Reported lesion symptoms include itching and burning; the lesion is described as rough or flaky and raised or bumpy; the condition has been present for about one day; the back of the torso is involved; a close-up photograph; female subject, age 40–49 — 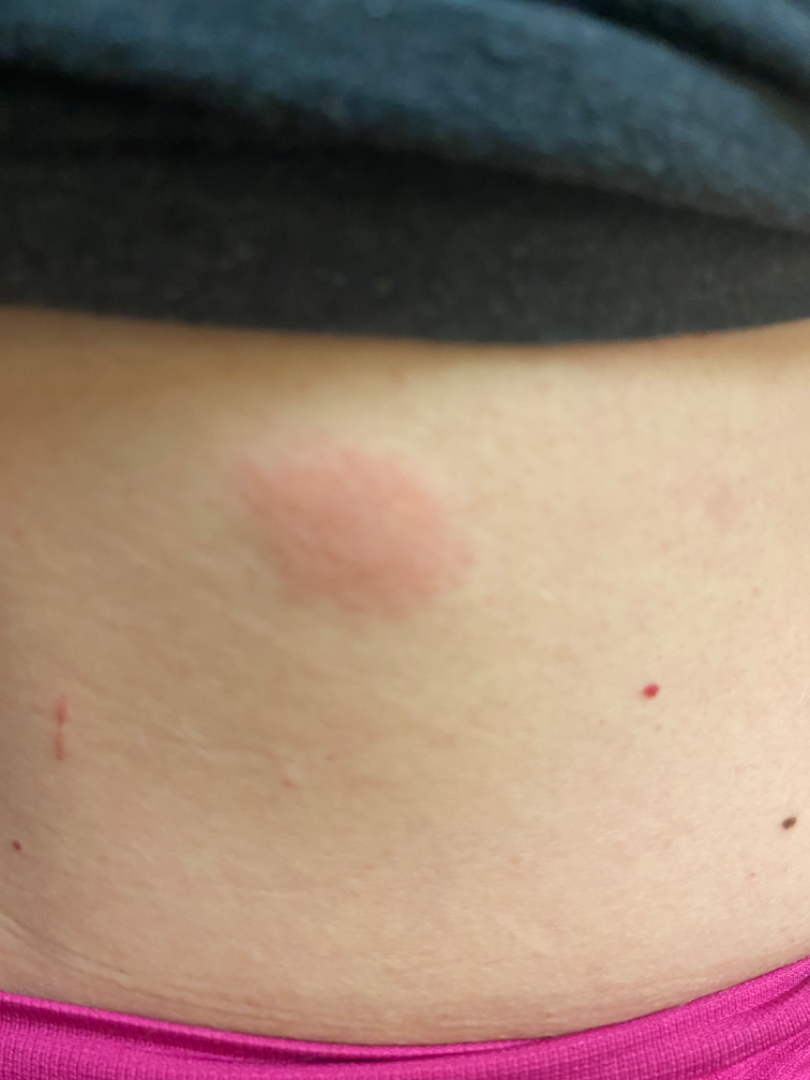diagnostic considerations = Insect Bite (favored); Urticaria (possible); Primary cutaneous lymphoma (unlikely); Cutaneous lupus (unlikely)